A skin lesion imaged with a dermatoscope: 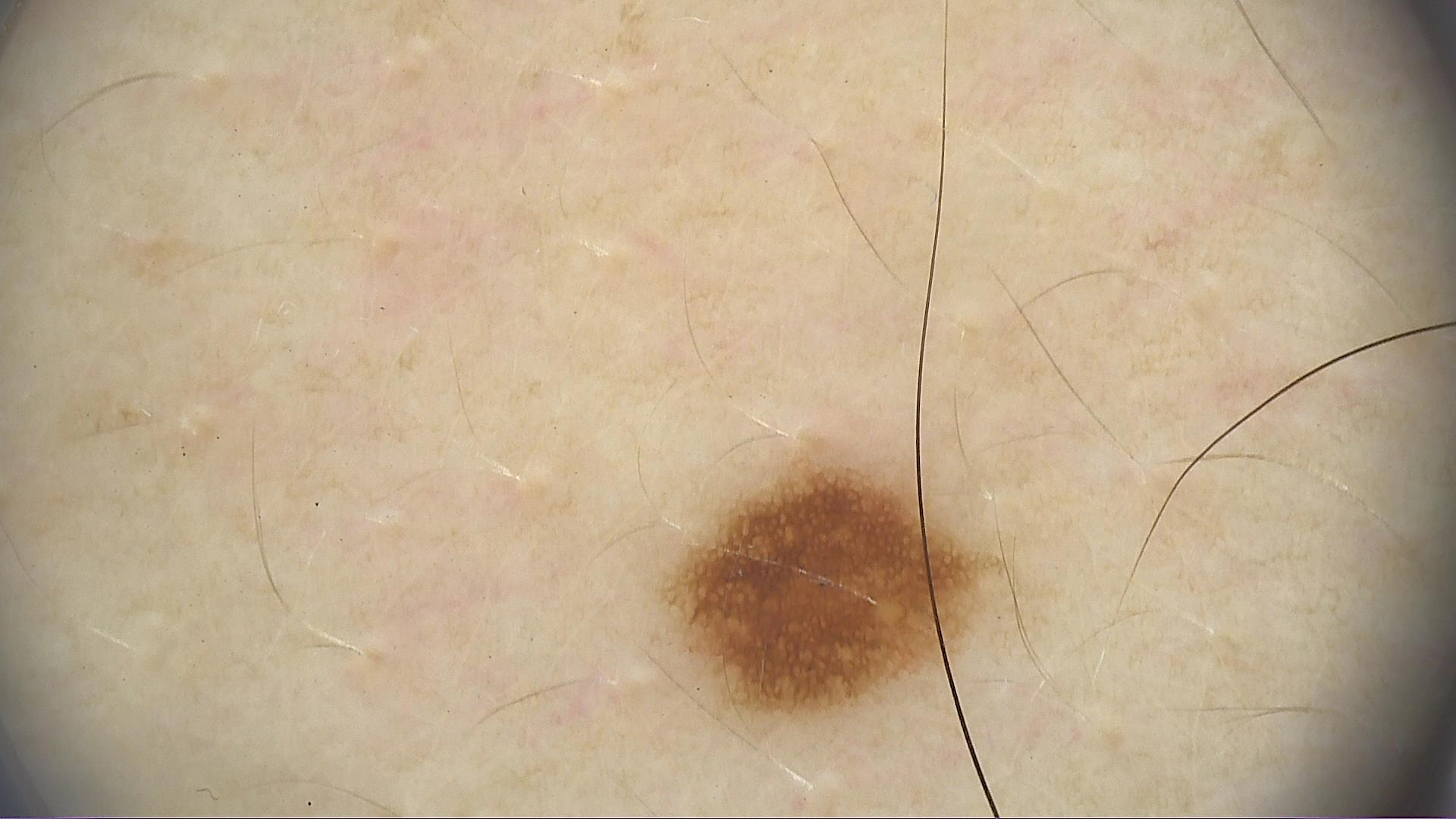  diagnosis:
    name: dysplastic junctional nevus
    code: jd
    malignancy: benign
    super_class: melanocytic
    confirmation: expert consensus